The photo was captured at a distance; the lesion involves the head or neck; male contributor, age 18–29:
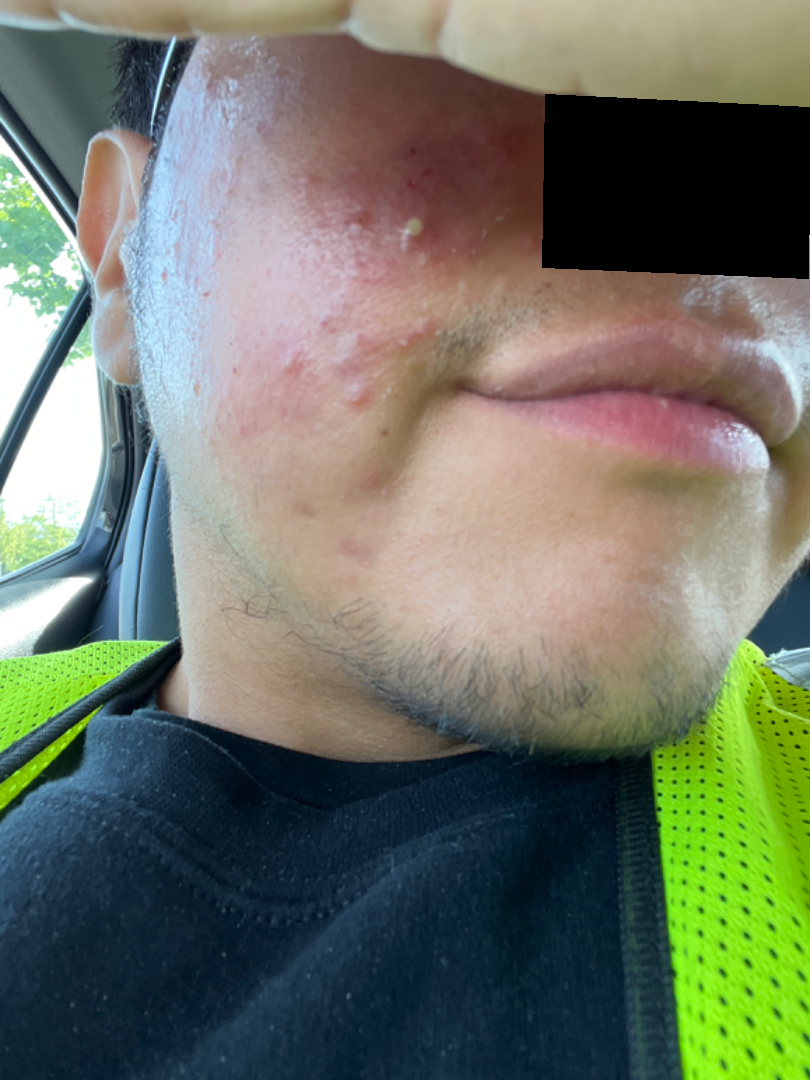Q: What conditions are considered?
A: the leading impression is Acne